A clinical photograph showing a skin lesion. A subject 73 years old — 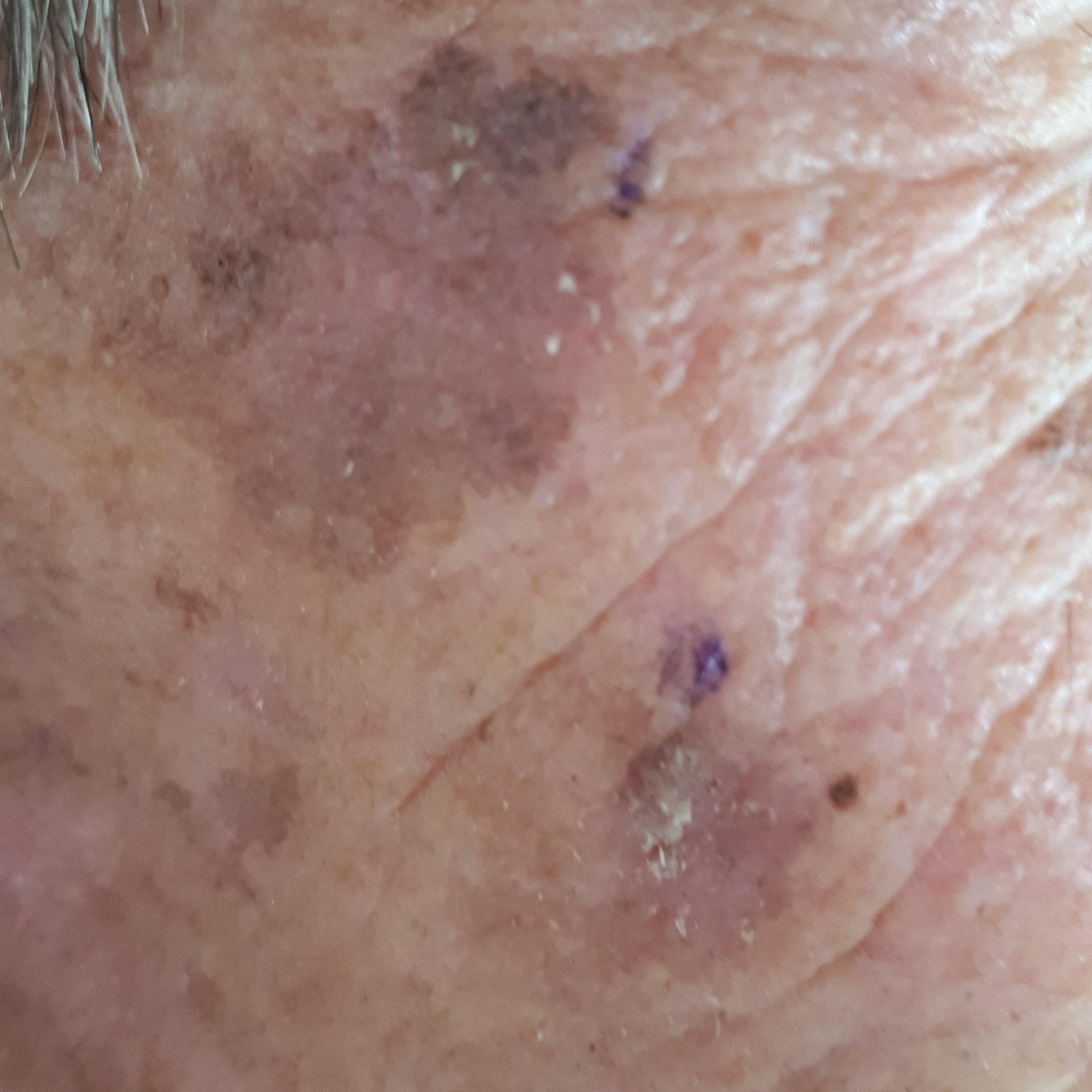location: the face; symptoms: itching, growth; assessment: actinic keratosis (clinical consensus).